A dermoscopy image of a single skin lesion:
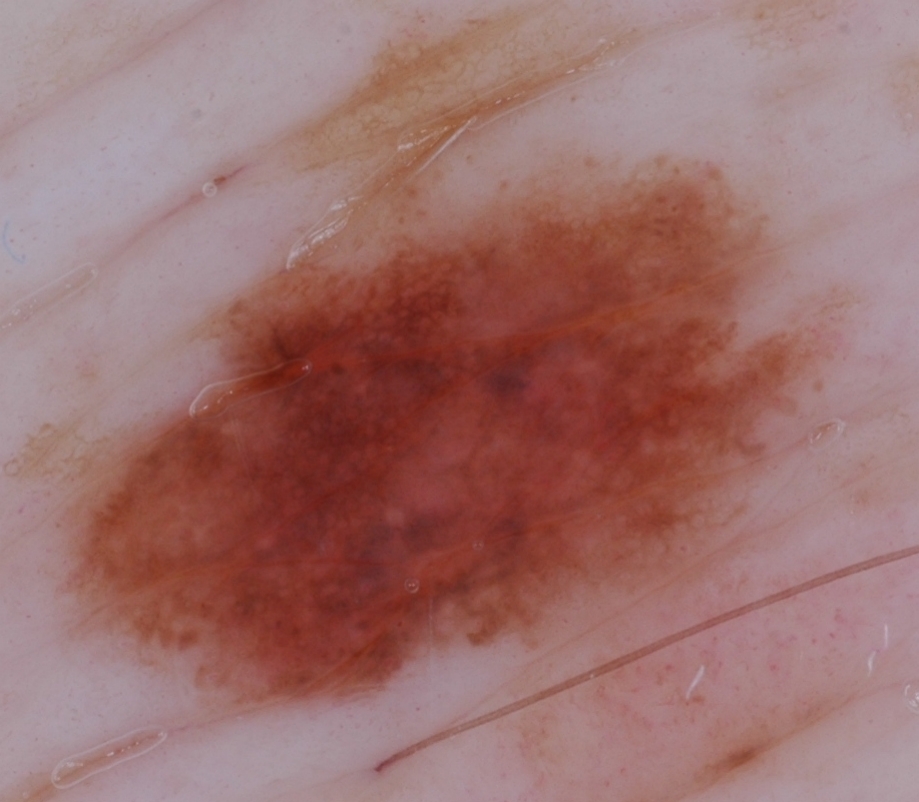Case summary:
The dermoscopic pattern shows globules and pigment network. The lesion reaches across nearly the entire image.
Conclusion:
Consistent with a melanocytic nevus, a benign lesion.